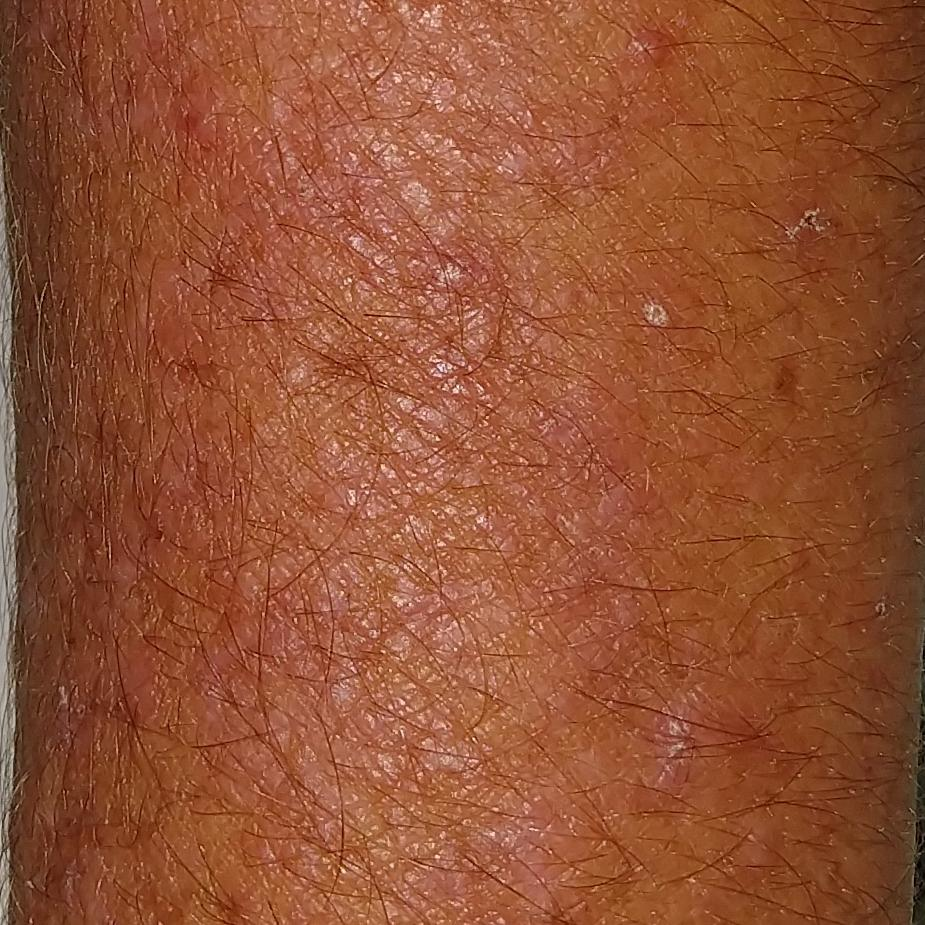Case:
- modality: clinical photo
- patient: 42 years old
- site: a forearm
- diagnostic label: actinic keratosis (clinical consensus)